The patient is Fitzpatrick phototype III. A female patient 58 years old — 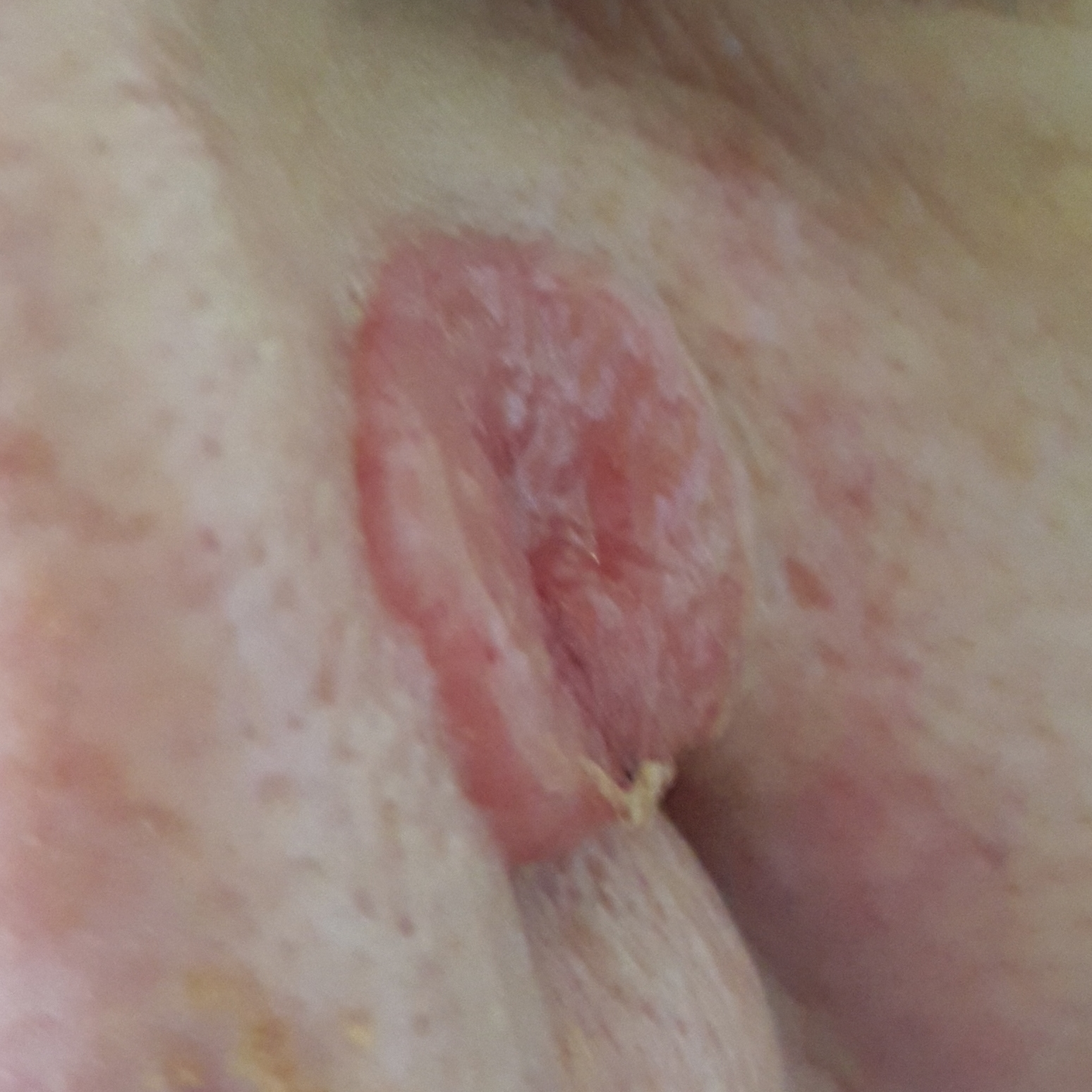{
  "lesion_location": "the nose",
  "lesion_size": {
    "diameter_1_mm": 17.0,
    "diameter_2_mm": 14.0
  },
  "symptoms": {
    "present": [
      "change in appearance",
      "bleeding",
      "pain",
      "elevation",
      "growth",
      "itching"
    ]
  },
  "diagnosis": {
    "name": "basal cell carcinoma",
    "code": "BCC",
    "malignancy": "malignant",
    "confirmation": "histopathology"
  }
}